The photograph was taken at a distance · the lesion involves the leg — 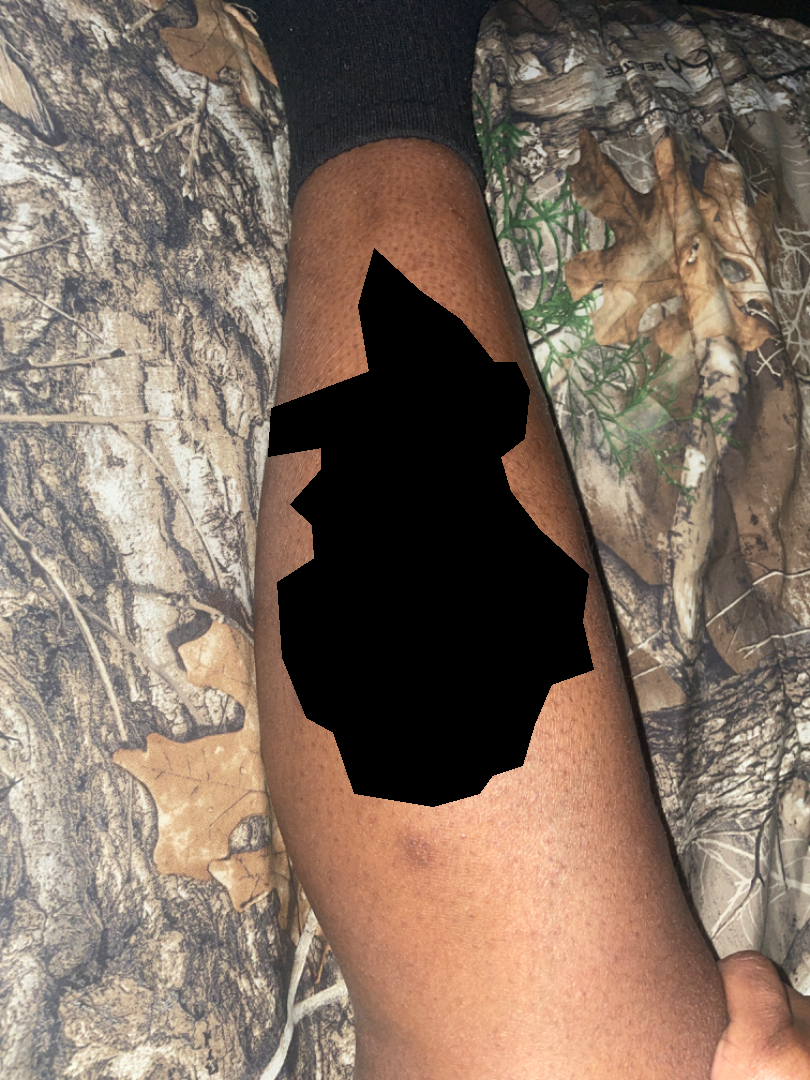The skin condition could not be confidently assessed from this image.
Present for one to three months.
FST IV.